The lesion is described as raised or bumpy · the patient considered this a rash · symptoms reported: enlargement, bothersome appearance and itching · the contributor is a female aged 50–59 · present for three to twelve months · the affected area is the leg · the photo was captured at a distance.
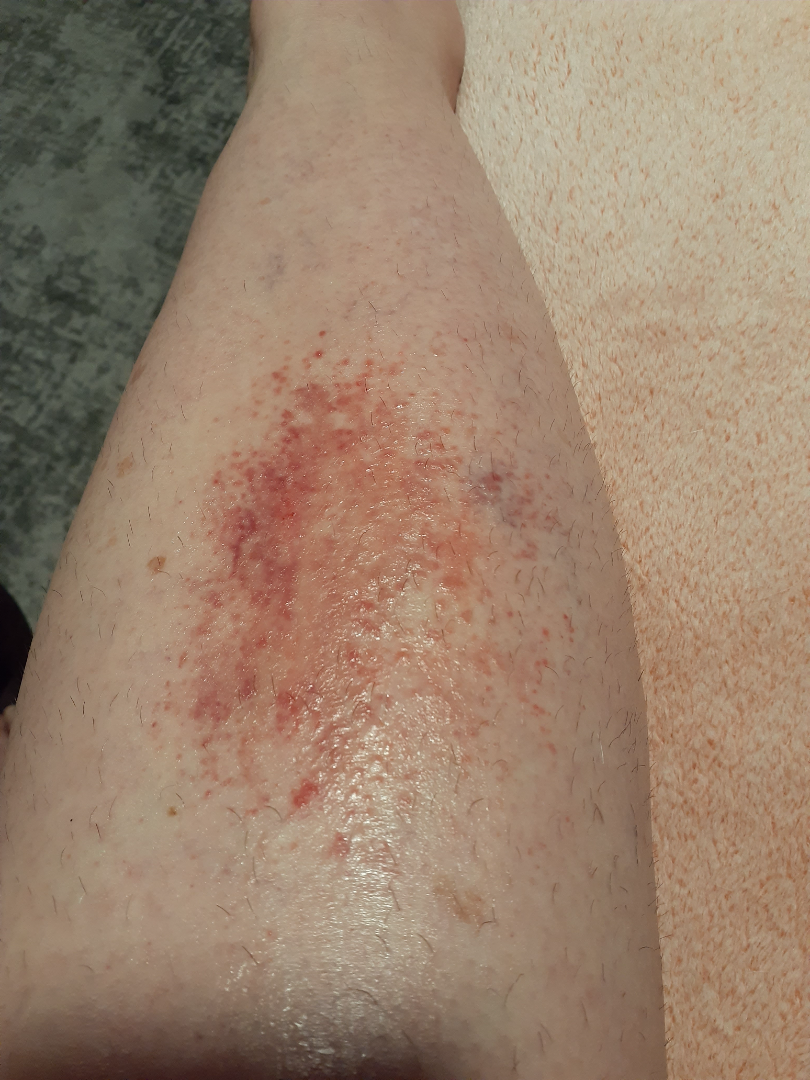differential:
  leading:
    - Allergic Contact Dermatitis
  unlikely:
    - Eczema
    - Stasis Dermatitis
    - Burn of skin
    - Acute dermatitis, NOS
    - Irritant Contact Dermatitis
    - Pretibial myxedema